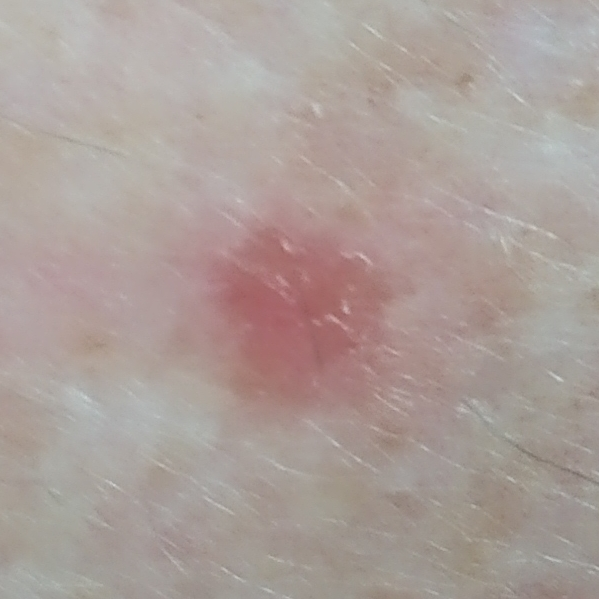The chart notes prior skin cancer (patient or family), alcohol use, pesticide exposure, no prior malignancy (patient or family), and no tobacco use. A male subject 58 years of age. A clinical photograph showing a skin lesion. Recorded as Fitzpatrick skin type II. The lesion involves the back. The lesion measures approximately 7 × 6 mm. The patient reports no symptoms. Histopathologically confirmed as an actinic keratosis.